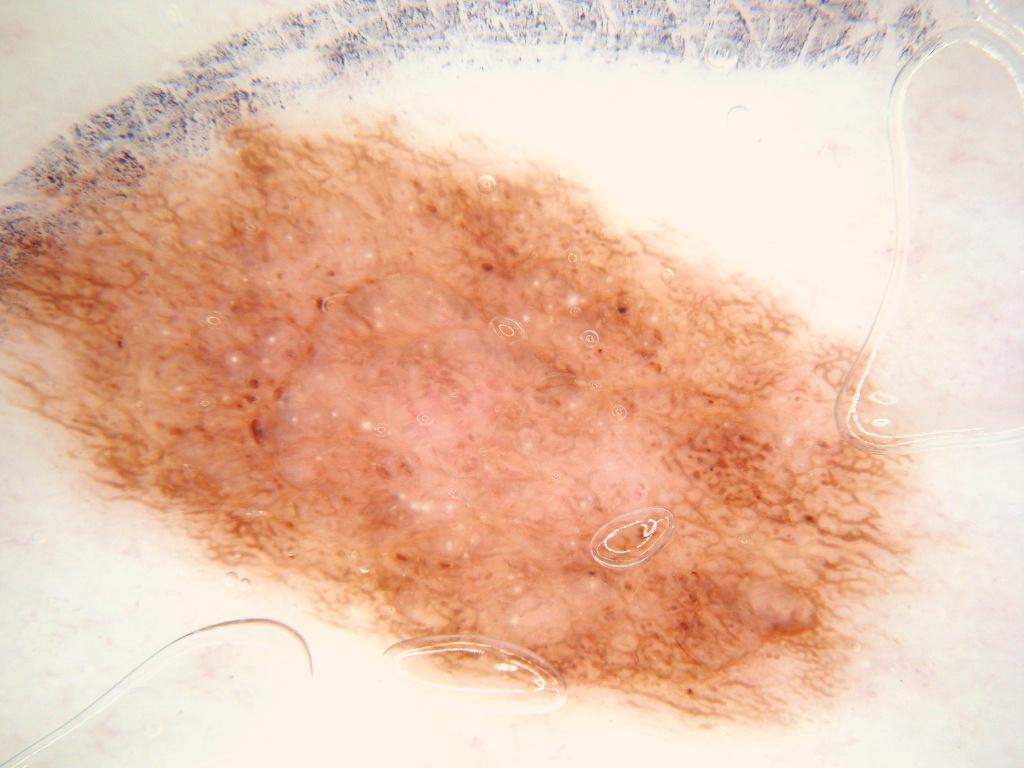  image:
    modality: dermoscopy
  lesion_extent: large
  dermoscopic_features:
    present:
      - pigment network
      - globules
      - milia-like cysts
    absent:
      - negative network
      - streaks
  lesion_location:
    bbox_xyxy:
      - 2
      - 106
      - 929
      - 738
  diagnosis:
    name: melanocytic nevus
    malignancy: benign
    lineage: melanocytic
    provenance: clinical